A moderate number of moles by the patient's own estimate — 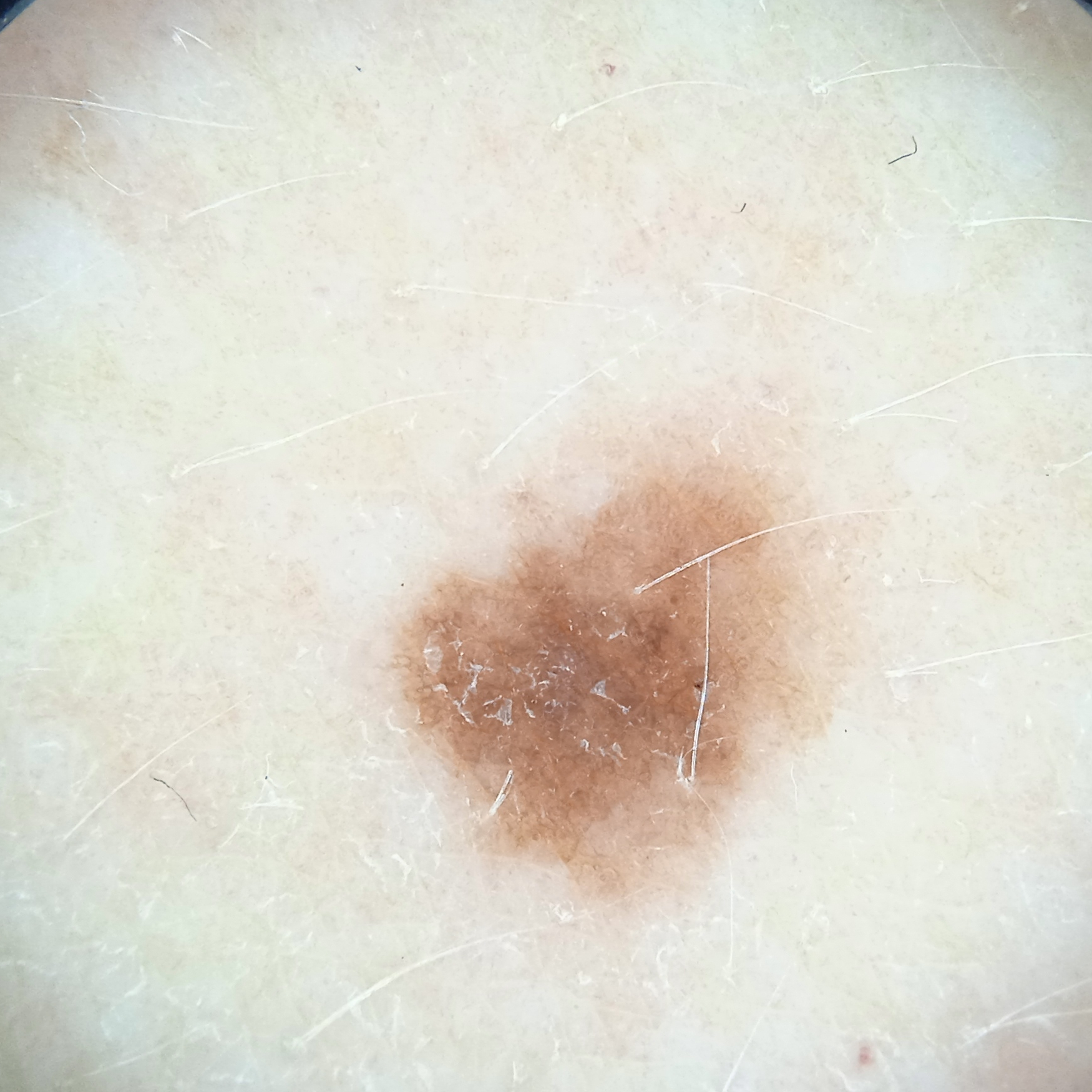Q: What is the anatomic site?
A: the torso
Q: What was the diagnosis?
A: melanocytic nevus (dermatologist consensus)